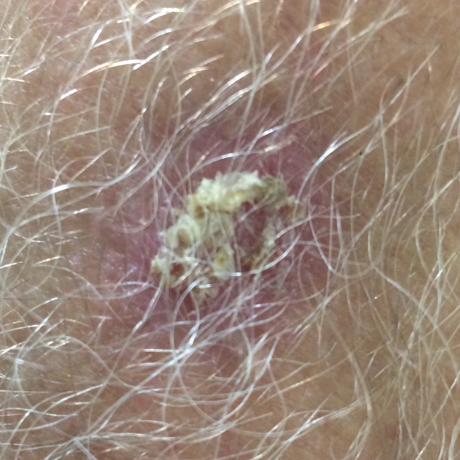Patient and lesion:
By history, alcohol use and pesticide exposure. A clinical photograph of a skin lesion. A male subject 56 years old. The lesion involves a forearm. The lesion measures approximately 20 × 15 mm.
Conclusion:
On biopsy, the diagnosis was a basal cell carcinoma.